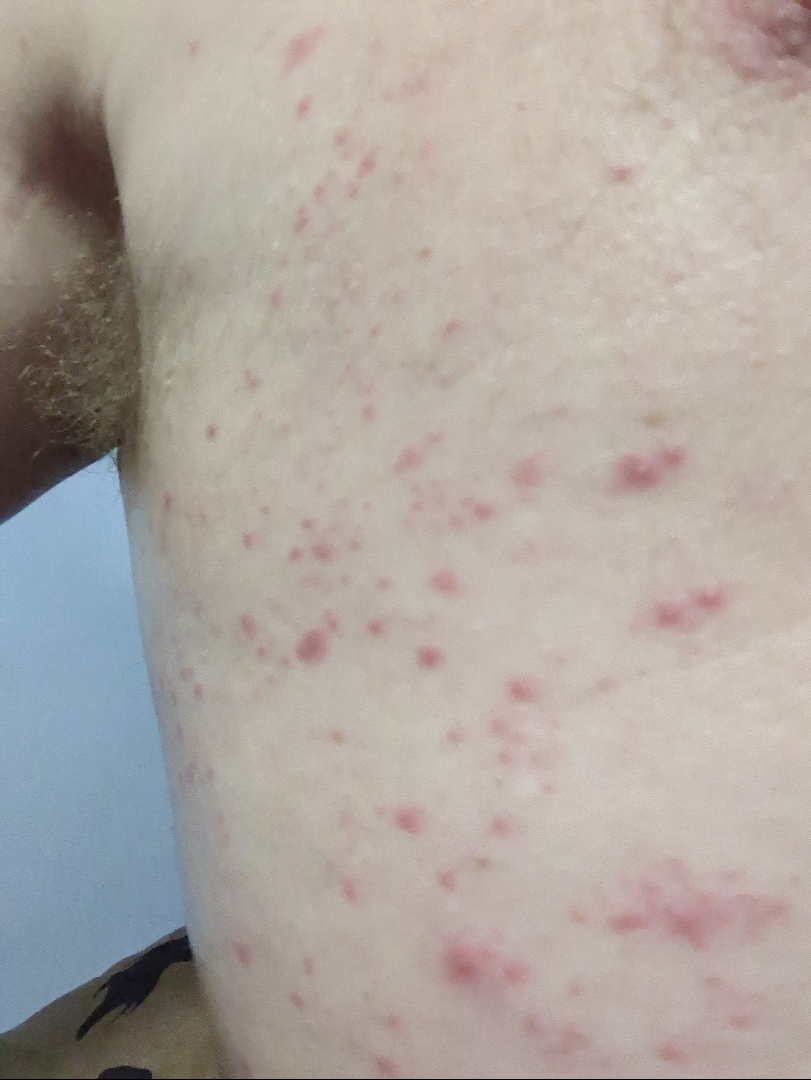  assessment: unable to determine
  symptoms:
    - enlargement
    - bothersome appearance
    - itching
  patient_category: a rash
  shot_type: at an angle
  systemic_symptoms:
    - joint pain
    - fatigue
  texture:
    - fluid-filled
    - raised or bumpy
  body_site:
    - back of the torso
    - front of the torso
  duration: about one day